The photo was captured at a distance; the subject is 60–69, female; located on the back of the torso: 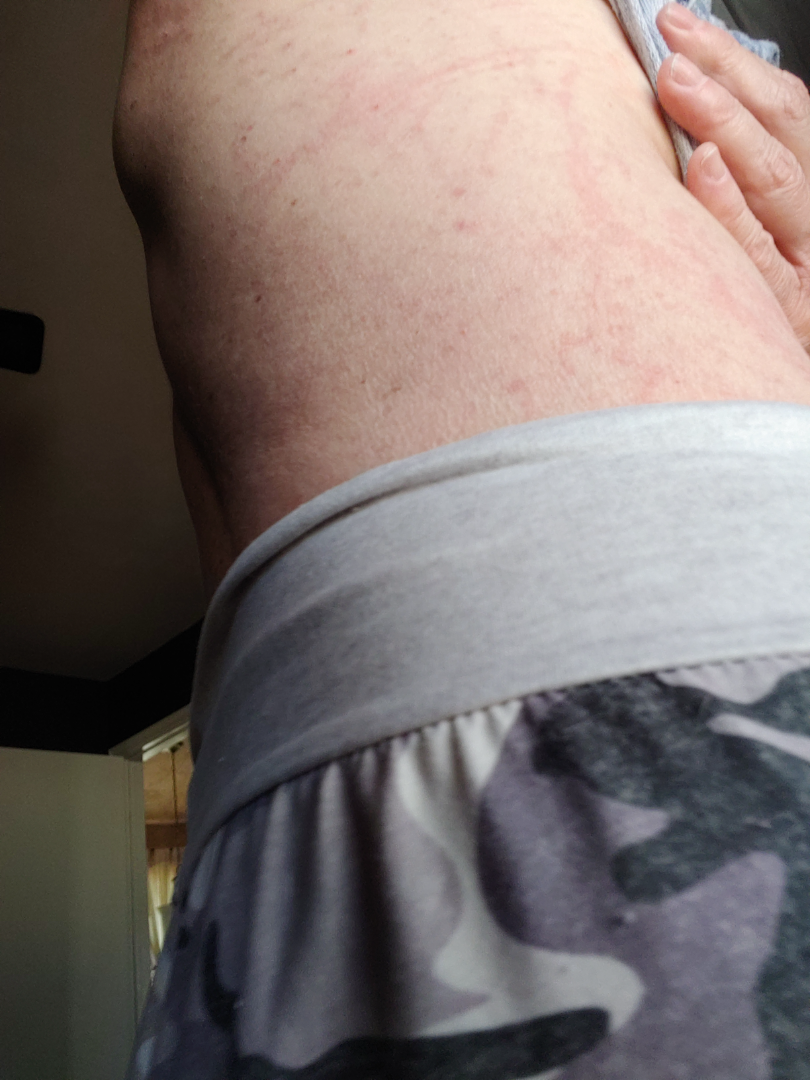On dermatologist assessment of the image, favoring Urticaria.